Symptoms reported: darkening, enlargement, itching and burning. The patient reported no systemic symptoms. The photo was captured at a distance. The arm is involved. The subject is 40–49, female. The contributor notes the condition has been present for one to four weeks. The patient considered this a rash — 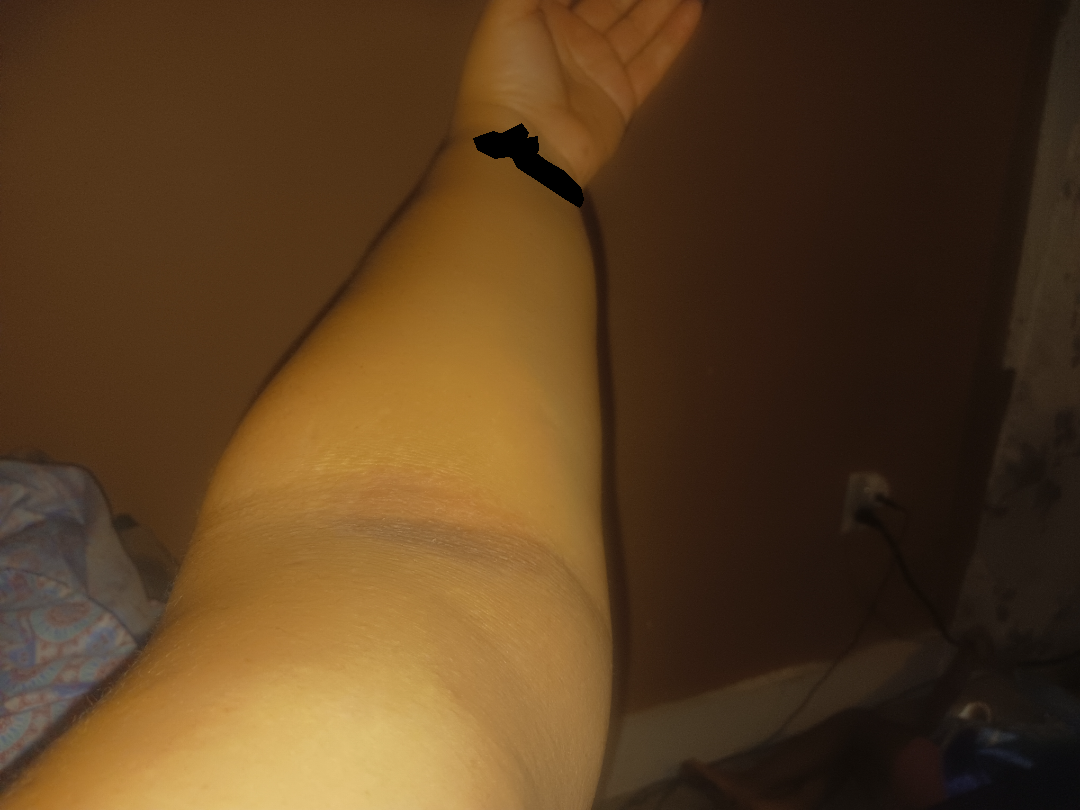No differential diagnosis could be assigned on photographic review.